A female patient aged 78; a clinical close-up of a skin lesion; the patient describes having numerous moles; the patient says their skin tans without first burning.
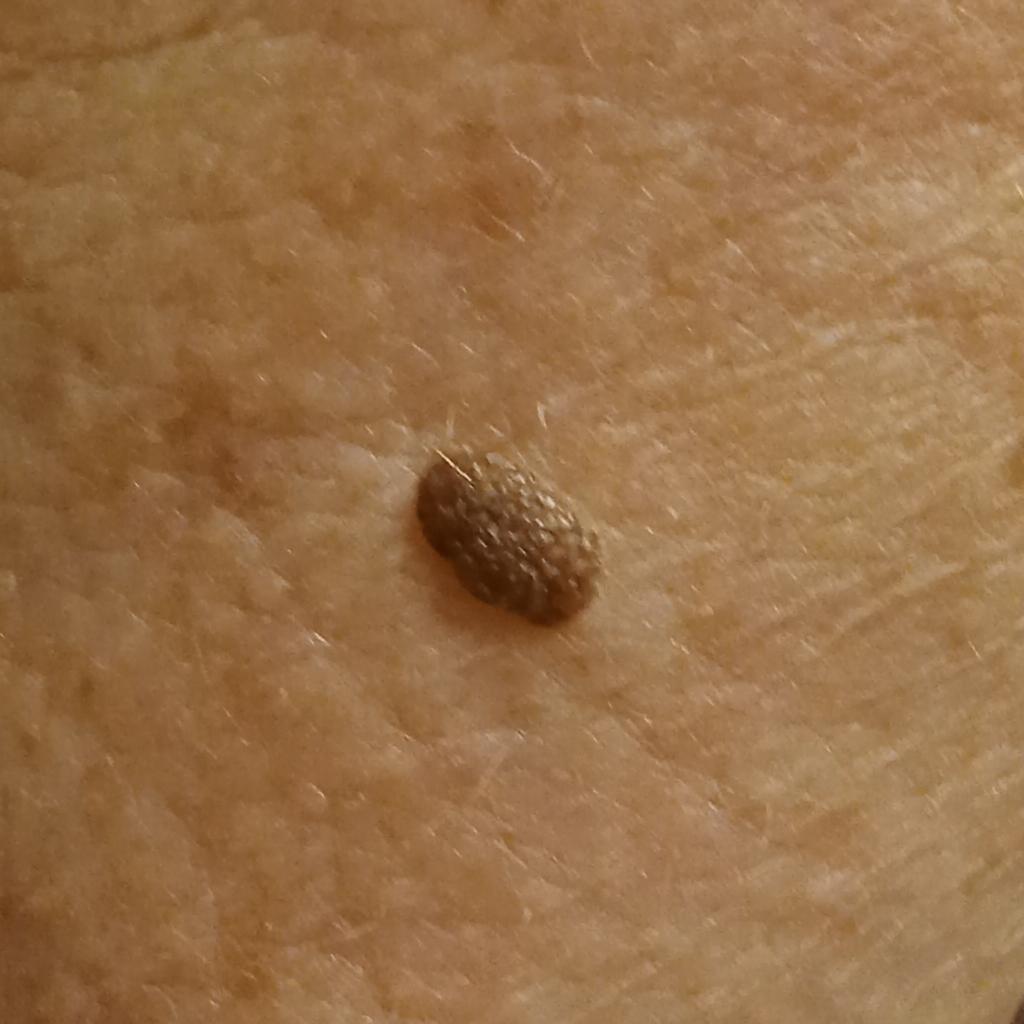– diameter — 5.6 mm
– diagnostic label — seborrheic keratosis (dermatologist consensus)